A male patient, in their mid-30s; a dermatoscopic image of a skin lesion.
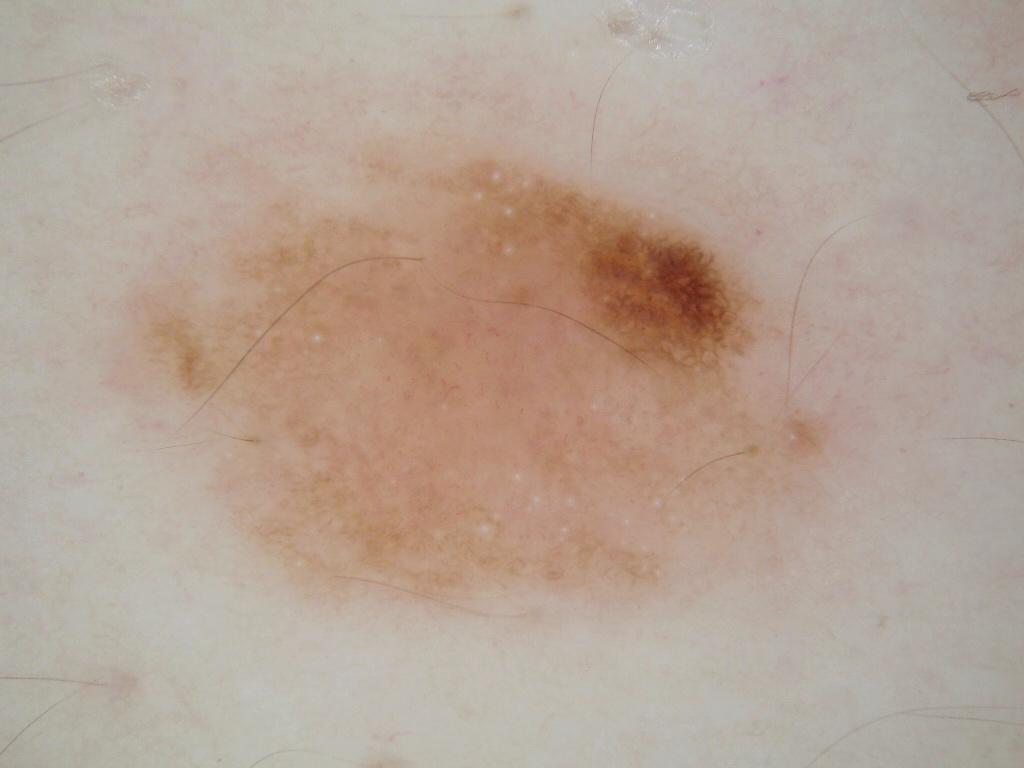Image and clinical context:
With coordinates (x1, y1, x2, y2), the lesion's extent is 108, 135, 827, 633. Dermoscopy demonstrates milia-like cysts and pigment network; no globules, negative network, or streaks. The lesion takes up about 35% of the image.
Impression:
Consistent with a melanocytic nevus, a benign lesion.